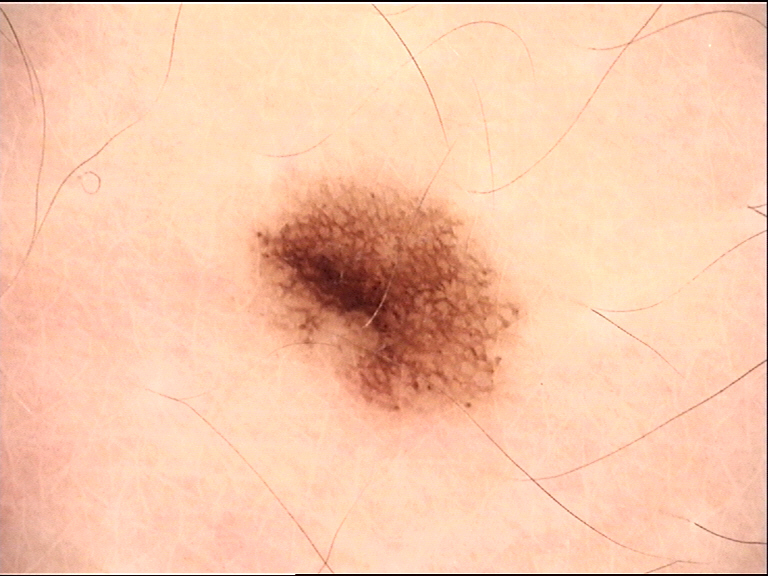Q: What is the imaging modality?
A: dermoscopy
Q: What is the lesion category?
A: banal
Q: What was the diagnostic impression?
A: junctional nevus (expert consensus)